The contributor reports the lesion is raised or bumpy. The patient is 18–29, female. This image was taken at a distance. The contributor reports itching, enlargement, bothersome appearance and darkening. Present for less than one week. The affected area is the leg. The patient considered this a rash:
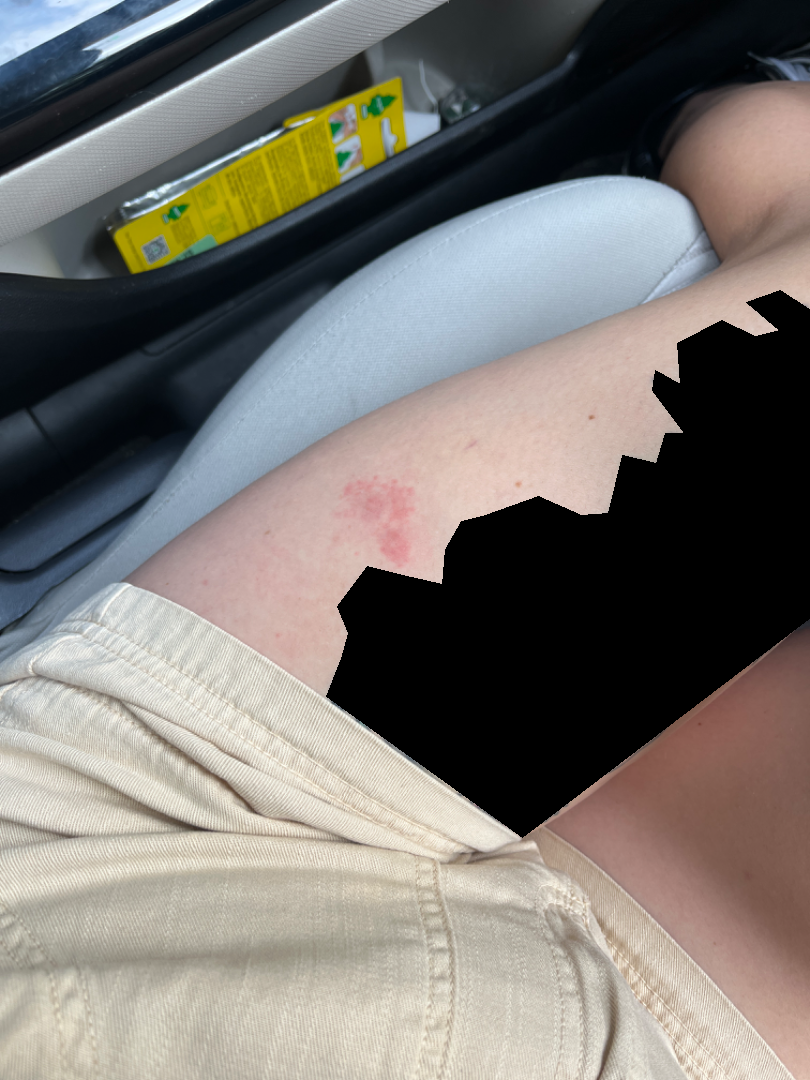Assessment:
Reviewed remotely by one dermatologist: Eczema and Allergic Contact Dermatitis were each considered, in no particular order.